The lesion is described as rough or flaky and raised or bumpy, the photo was captured at a distance, present for one to four weeks, the contributor reports burning and itching, FST II; lay reviewers estimated MST 4 (US pool) or 2 (India pool), the affected area is the arm — 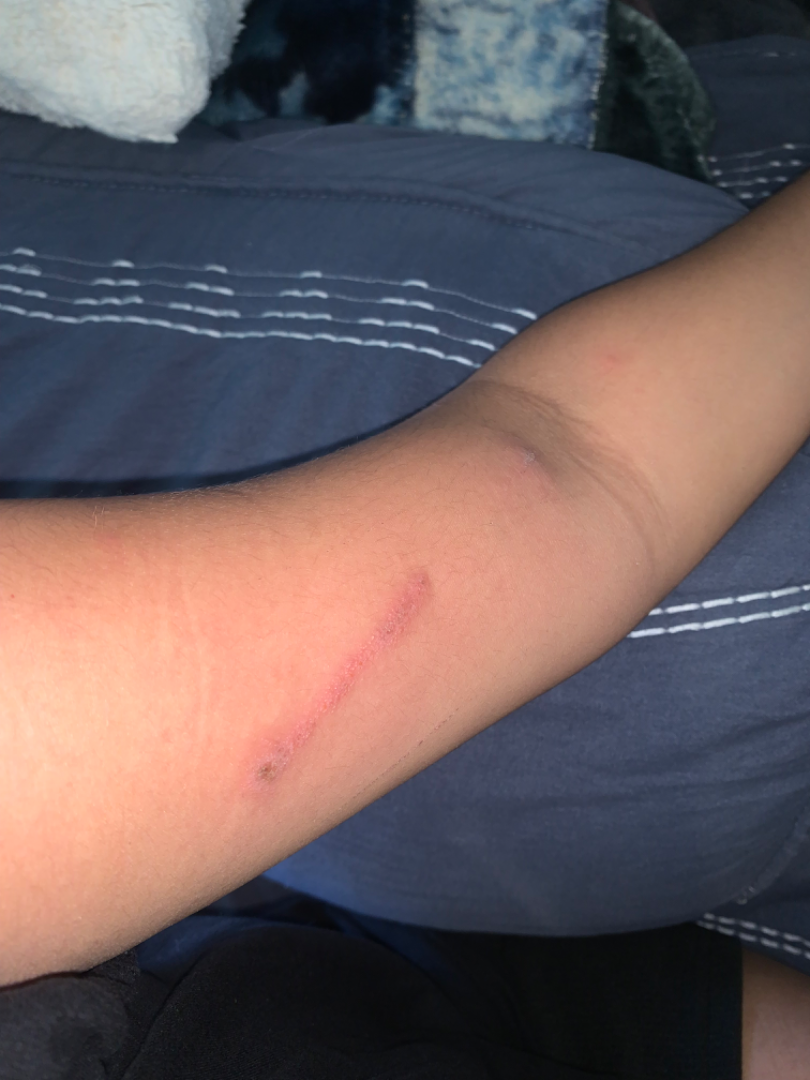On remote dermatologist review, the primary impression is wound/abrasion; also raised was Allergic Contact Dermatitis; less likely is Skin and soft tissue atypical mycobacterial infection.